The back of the torso, head or neck, arm and front of the torso are involved · the patient is 18–29, female · a close-up photograph: 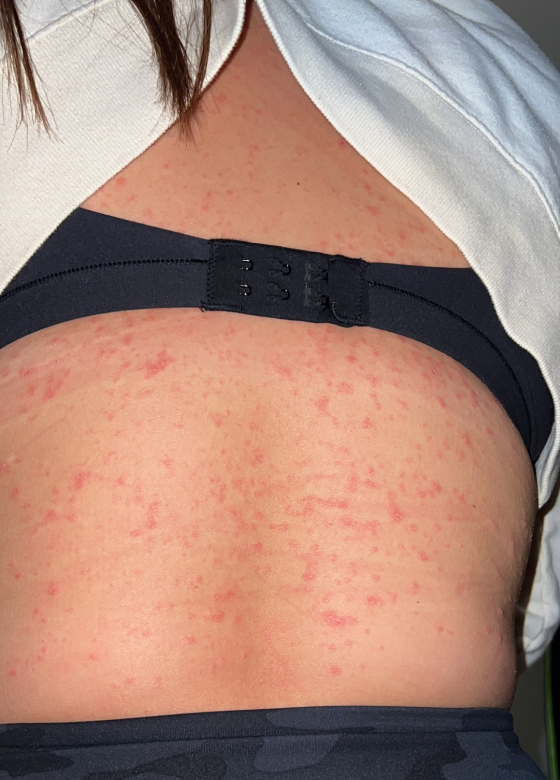Case summary:
– assessment · indeterminate from the photograph